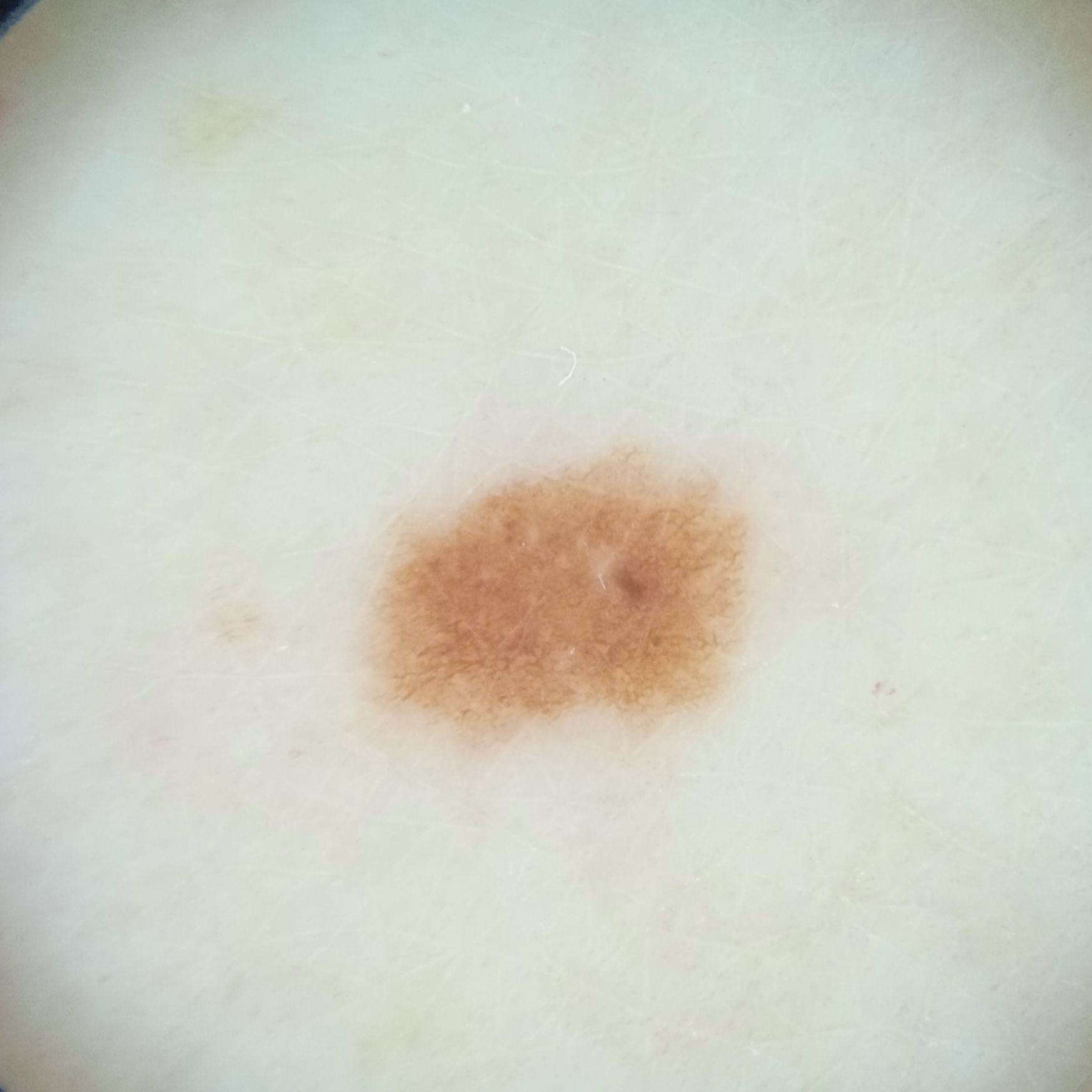Case summary: The patient says their skin tans without first burning. A female patient 67 years old. Few moles overall by the patient's own estimate. A dermatoscopic image of a skin lesion. On a questionnaire the patient reported no prior organ transplant and no personal history of skin cancer. Collected as part of a research study, without a referral diagnosis. The lesion is located on an arm. The lesion measures approximately 4.9 mm. Conclusion: The lesion was assessed as a melanocytic nevus.